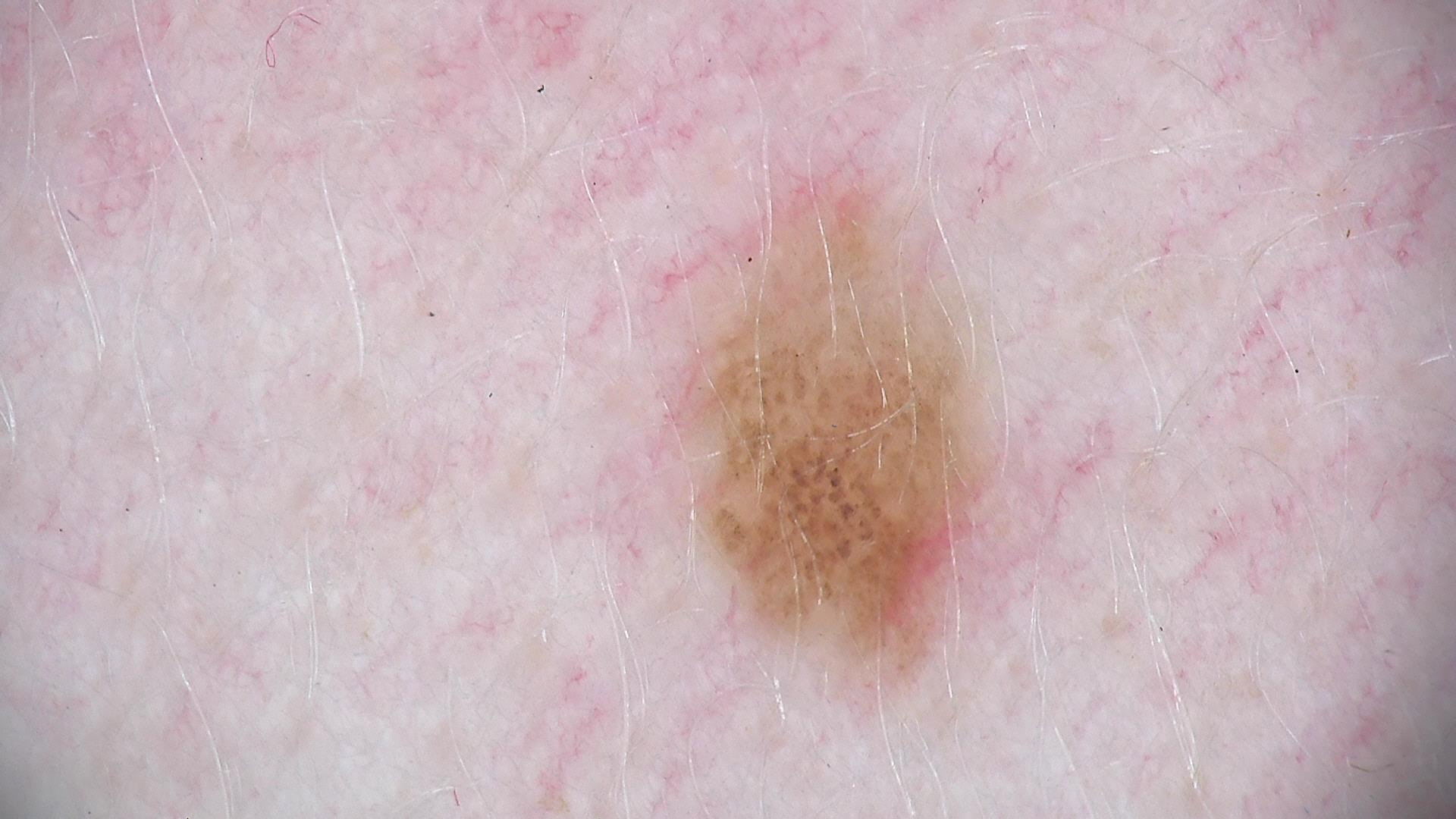Findings:
- imaging · dermoscopy
- class · compound nevus (expert consensus)